Self-categorized by the patient as a growth or mole. FST III; non-clinician graders estimated Monk Skin Tone 2. Female contributor, age 50–59. The lesion is associated with darkening, bothersome appearance and itching. No relevant systemic symptoms. Located on the arm. The photo was captured at a distance. Reported duration is three to twelve months. The contributor notes the lesion is raised or bumpy and rough or flaky — 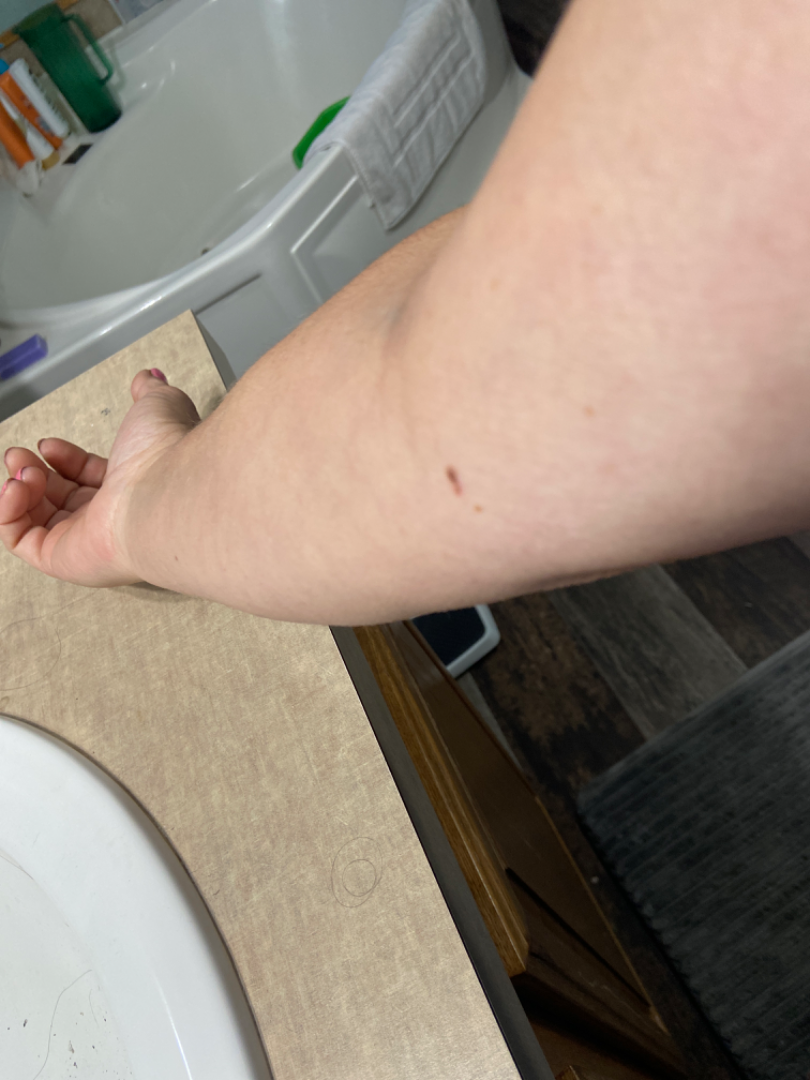assessment — unable to determine.